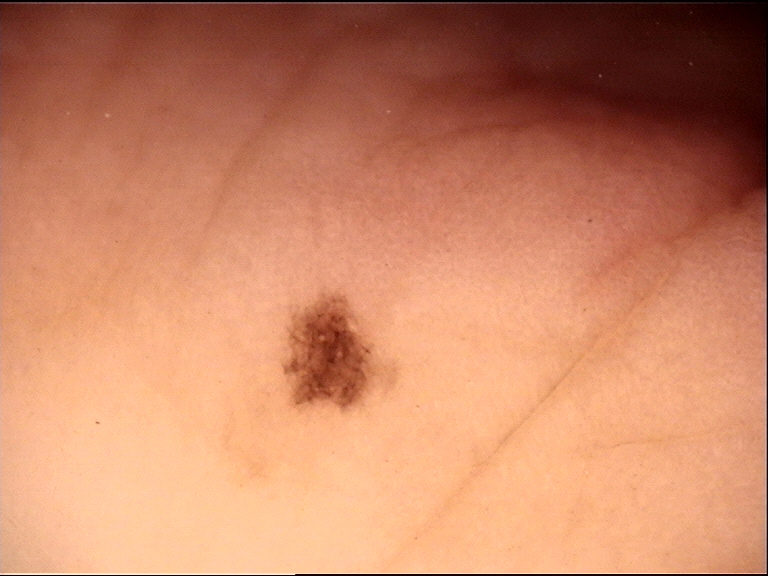Findings:
– imaging: dermoscopy
– lesion type: banal
– class: acral junctional nevus (expert consensus)